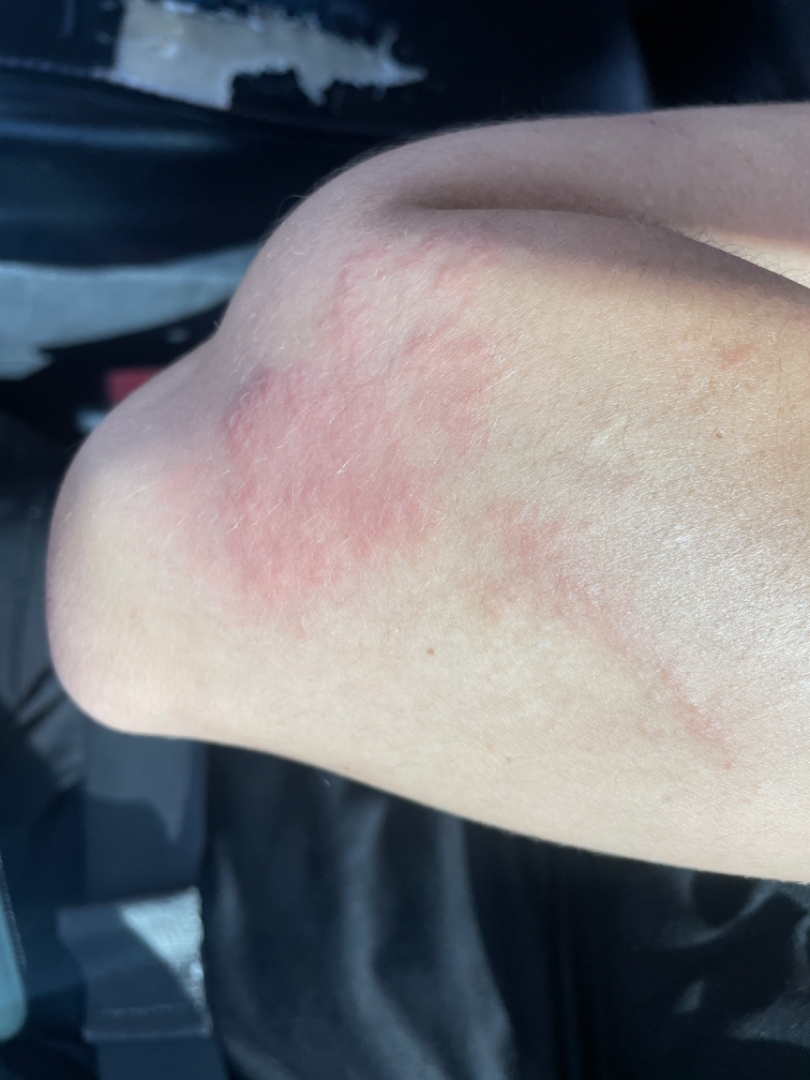Case summary:
- assessment: Allergic Contact Dermatitis (most likely); Herpes Simplex (considered); Herpes Zoster (lower probability)